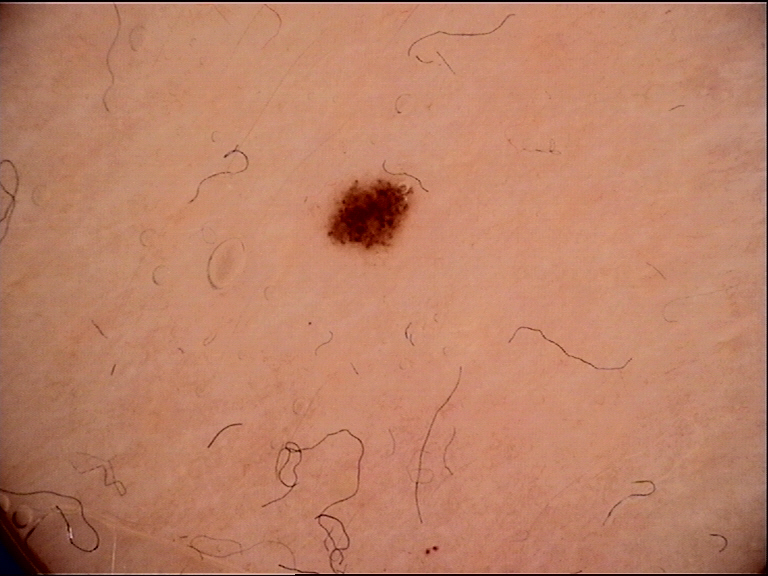- imaging — dermoscopy
- diagnostic label — dysplastic junctional nevus (expert consensus)